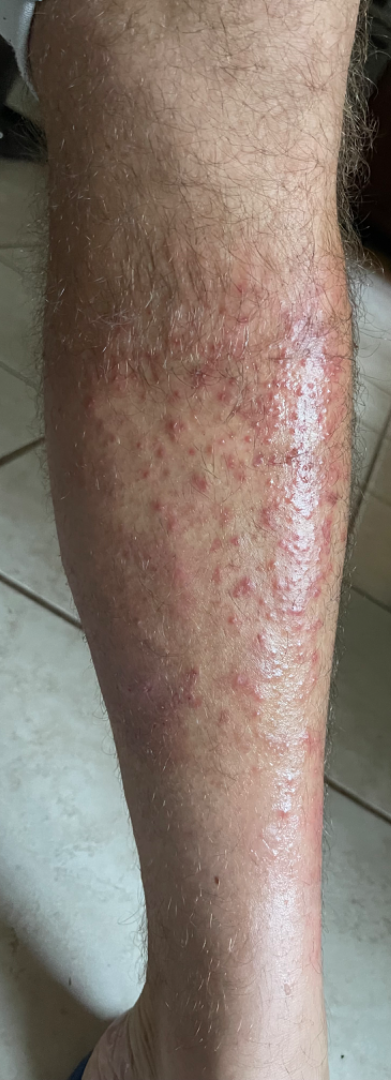The lesion involves the leg. This image was taken at an angle. On remote review of the image: the differential is split between Insect Bite and Allergic Contact Dermatitis.